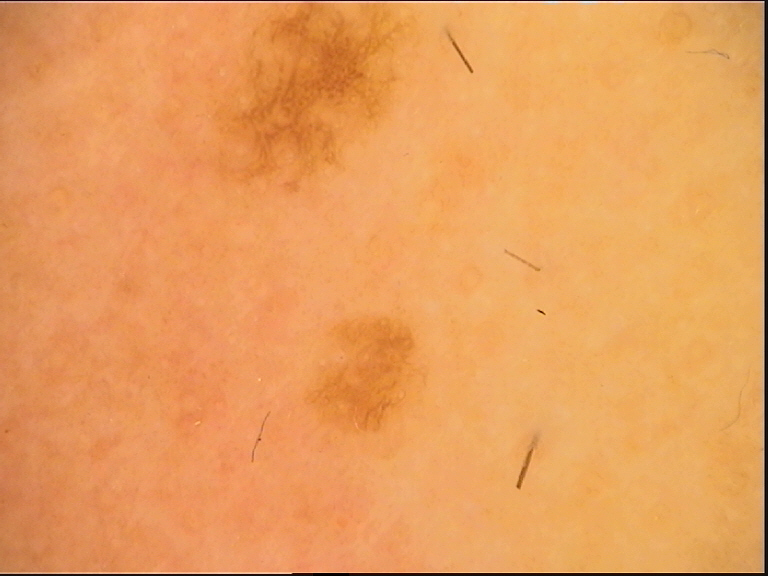image type — dermoscopy; diagnosis — dysplastic junctional nevus (expert consensus).